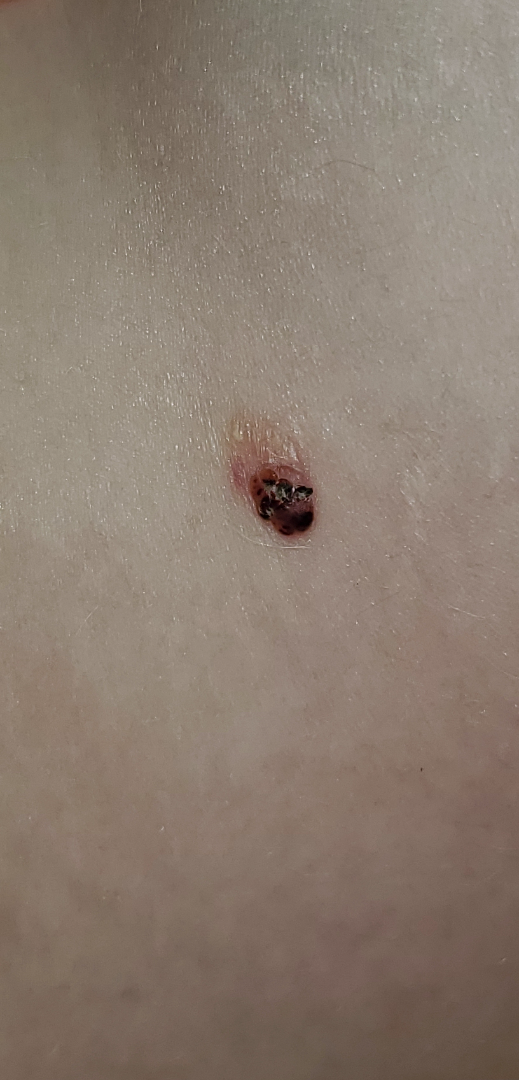shot_type: close-up
patient_category: skin that appeared healthy to them
skin_tone:
  fitzpatrick: I
duration: more than five years
systemic_symptoms: fatigue
body_site: leg
symptoms: bothersome appearance
texture:
  - rough or flaky
  - fluid-filled
  - raised or bumpy
differential:
  leading:
    - Insect Bite